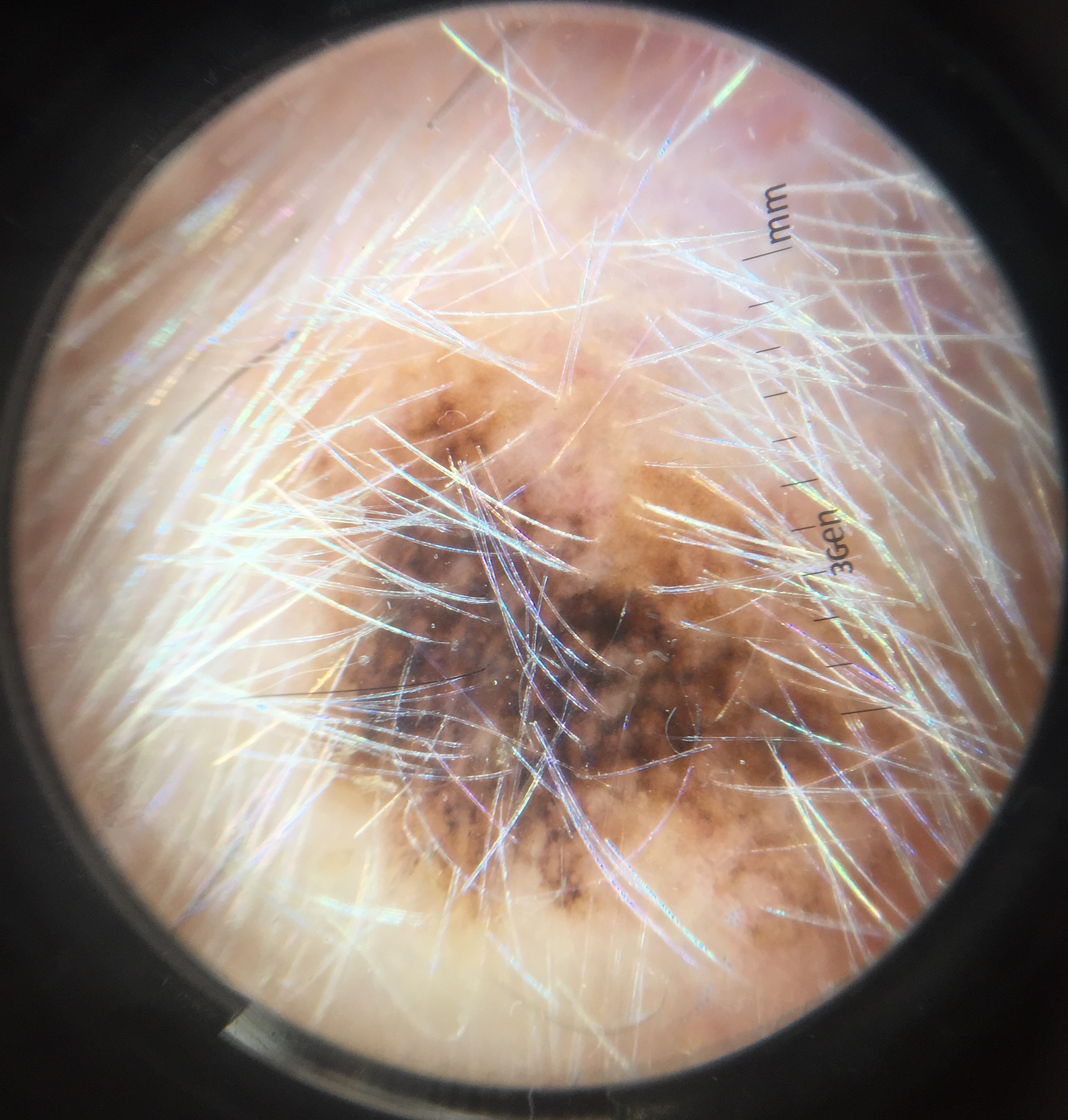diagnosis: melanoma (biopsy-proven)